Imaged for a research study, with no referral diagnosis recorded · a dermoscopy image of a skin lesion · a male patient 72 years old — 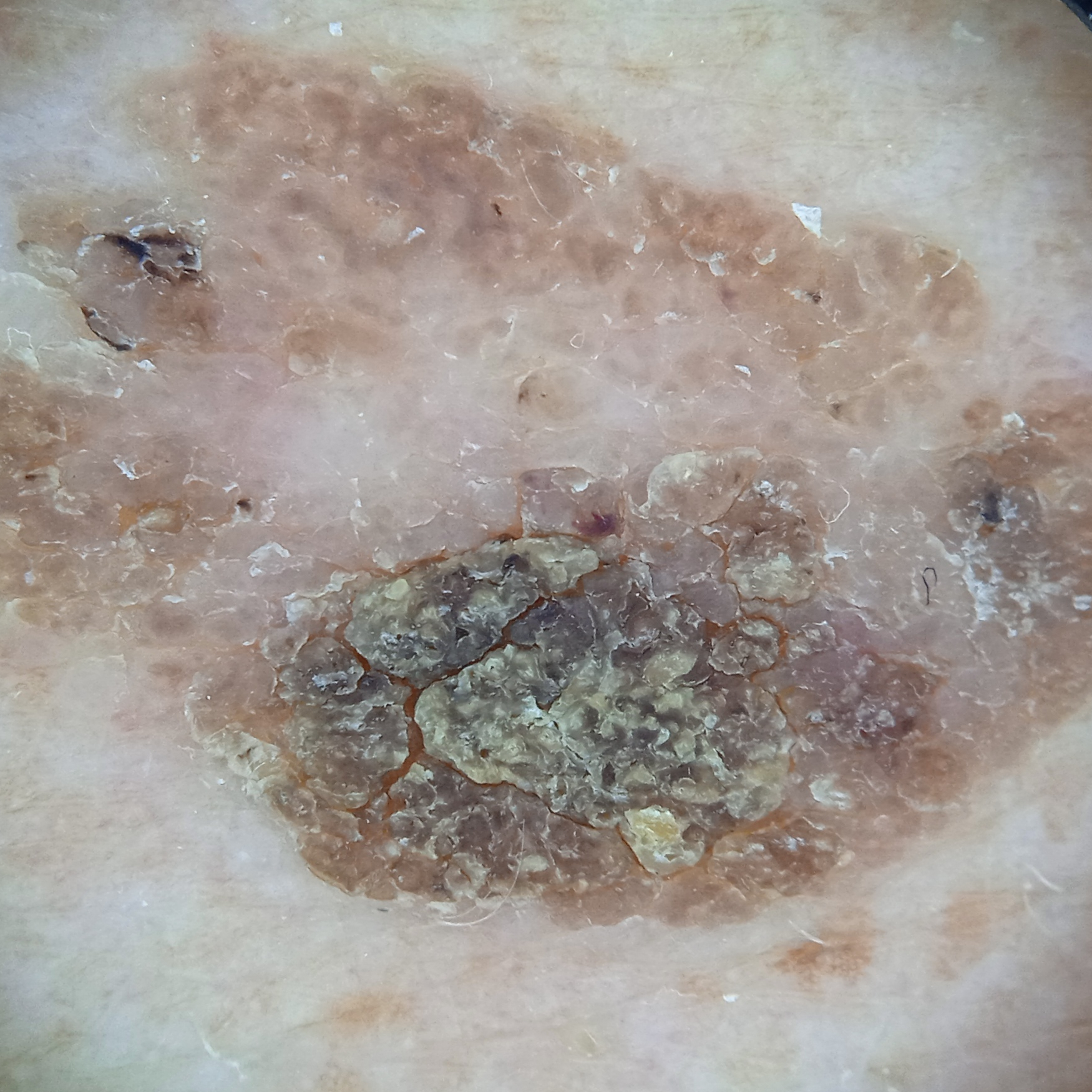| field | value |
|---|---|
| location | the back |
| lesion size | 13.7 mm |
| assessment | seborrheic keratosis (dermatologist consensus) |